A dermoscopic view of a skin lesion.
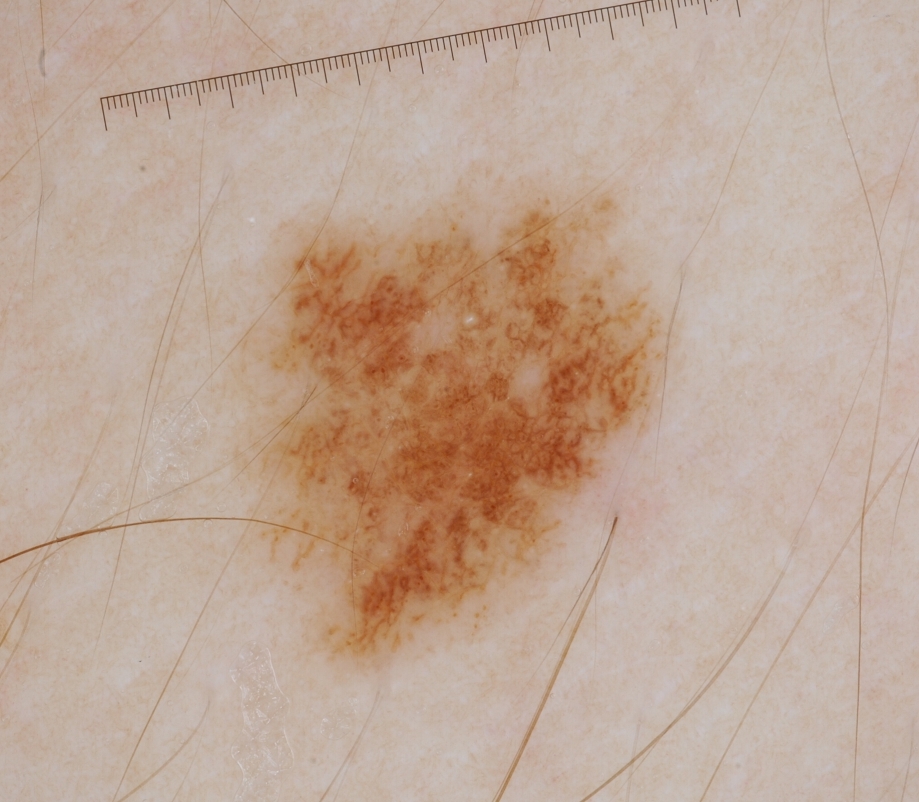With coordinates (x1, y1, x2, y2), the lesion's extent is [217, 160, 695, 681]. Dermoscopically, the lesion shows globules and pigment network; no milia-like cysts, negative network, or streaks. Consistent with a melanocytic nevus.